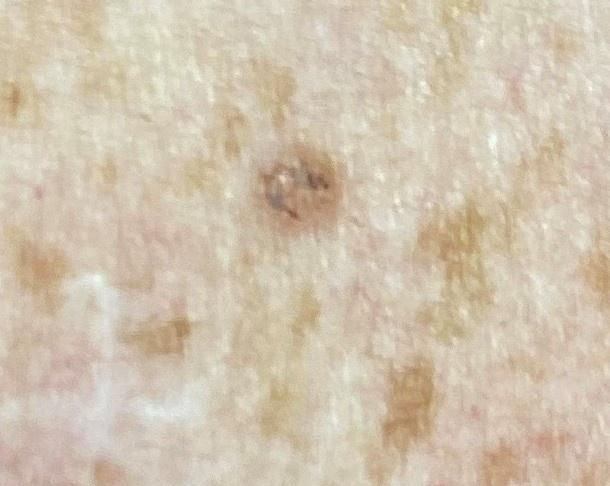Notes:
• modality — clinical overview photograph
• relevant background — no prior melanoma and no first-degree relative with melanoma
• Fitzpatrick — II
• site — the trunk
• diagnosis — Basal cell carcinoma (biopsy-proven)